The contributor is 18–29, female · this is a close-up image · the affected area is the back of the hand: 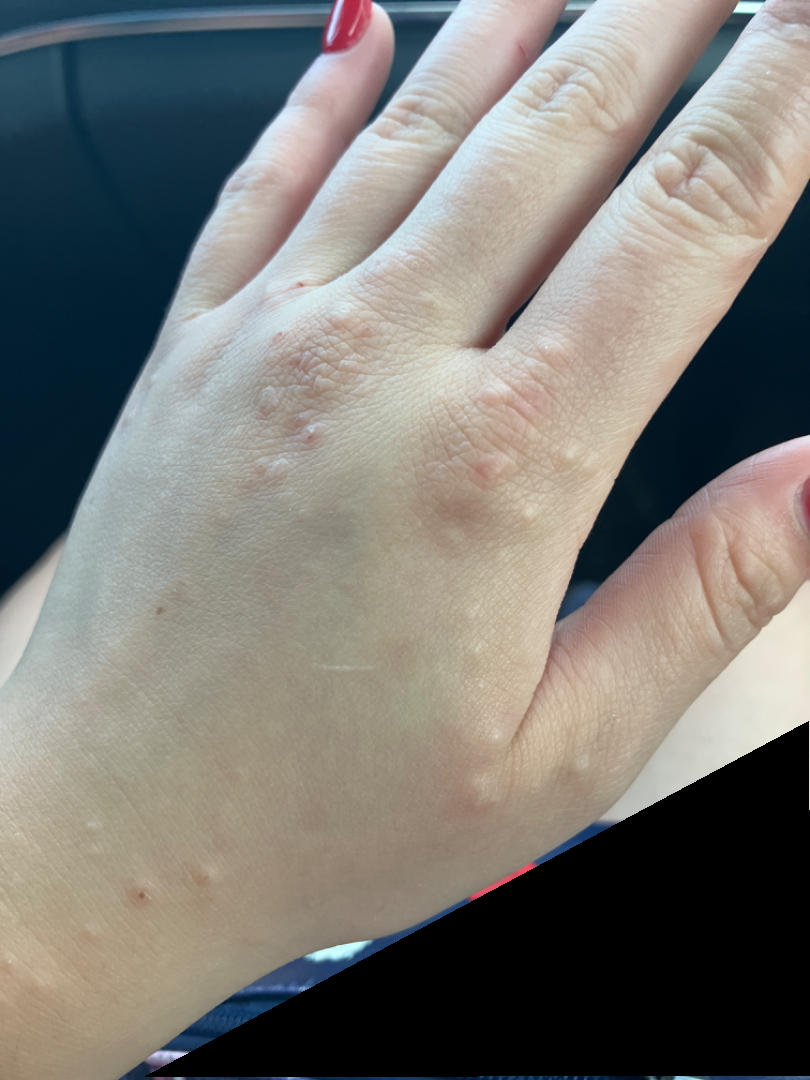The condition could not be reliably identified from the image. Self-categorized by the patient as a rash. Reported lesion symptoms include burning, bothersome appearance, itching, enlargement and pain. The lesion is described as fluid-filled, raised or bumpy and rough or flaky. Skin tone: Fitzpatrick II; human graders estimated a Monk Skin Tone of 1.